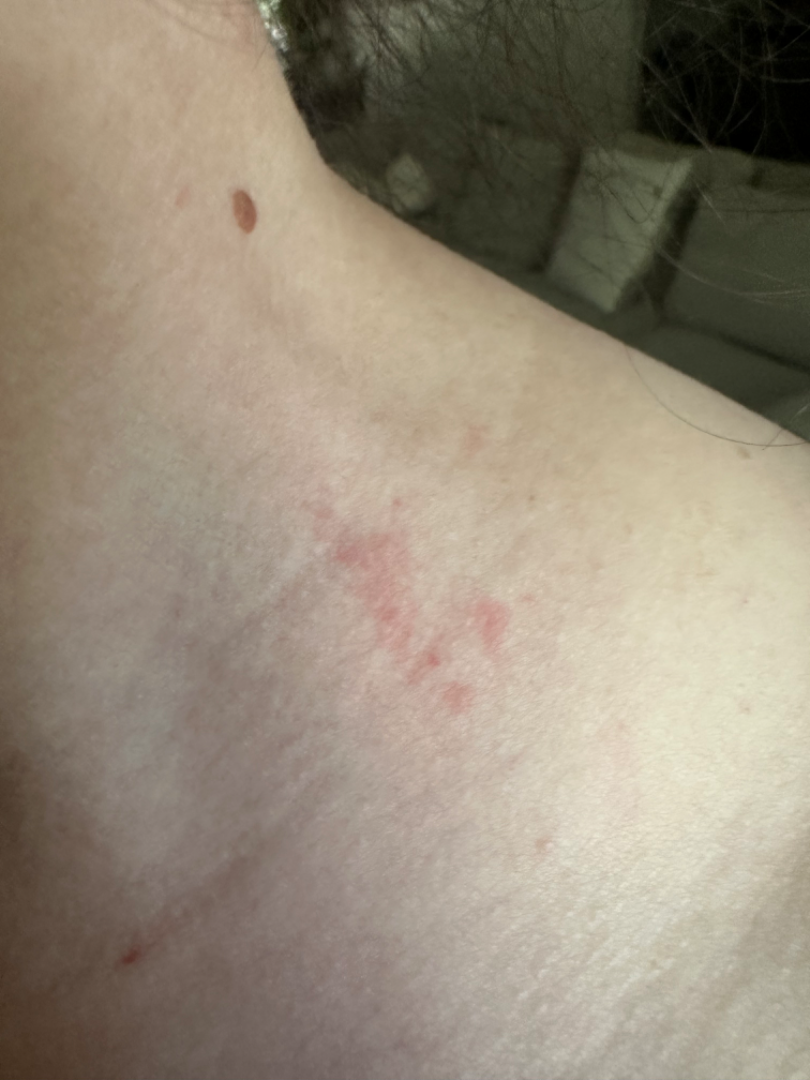The skin condition could not be confidently assessed from this image.
The lesion is described as raised or bumpy.
An image taken at an angle.
Located on the head or neck.
The contributor reports the condition has been present for about one day.